A clinical photograph showing a skin lesion in context:
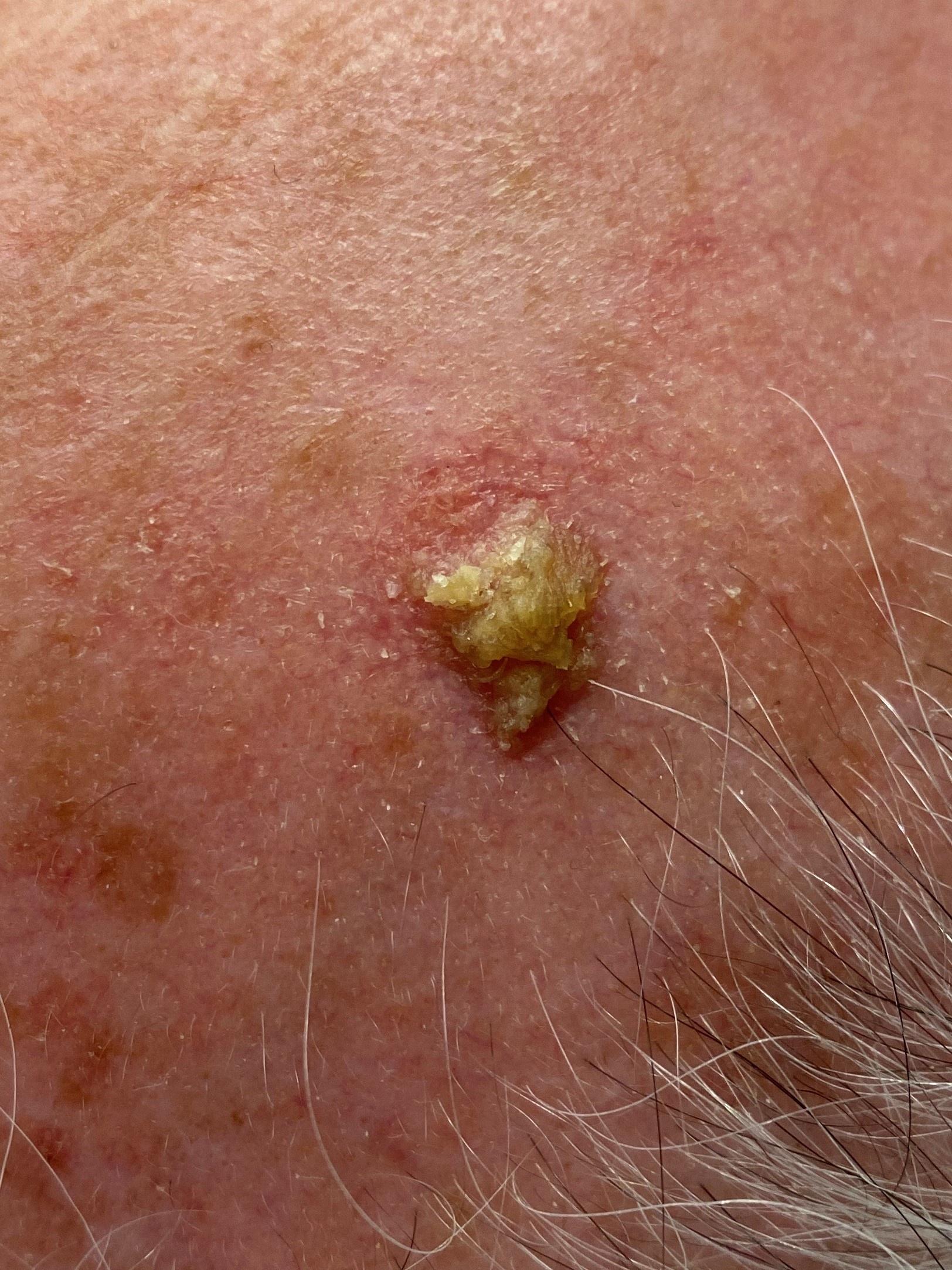The lesion involves the head or neck. Histopathological examination showed an epidermal proliferation — a squamous cell carcinoma.